A skin lesion imaged with a dermatoscope.
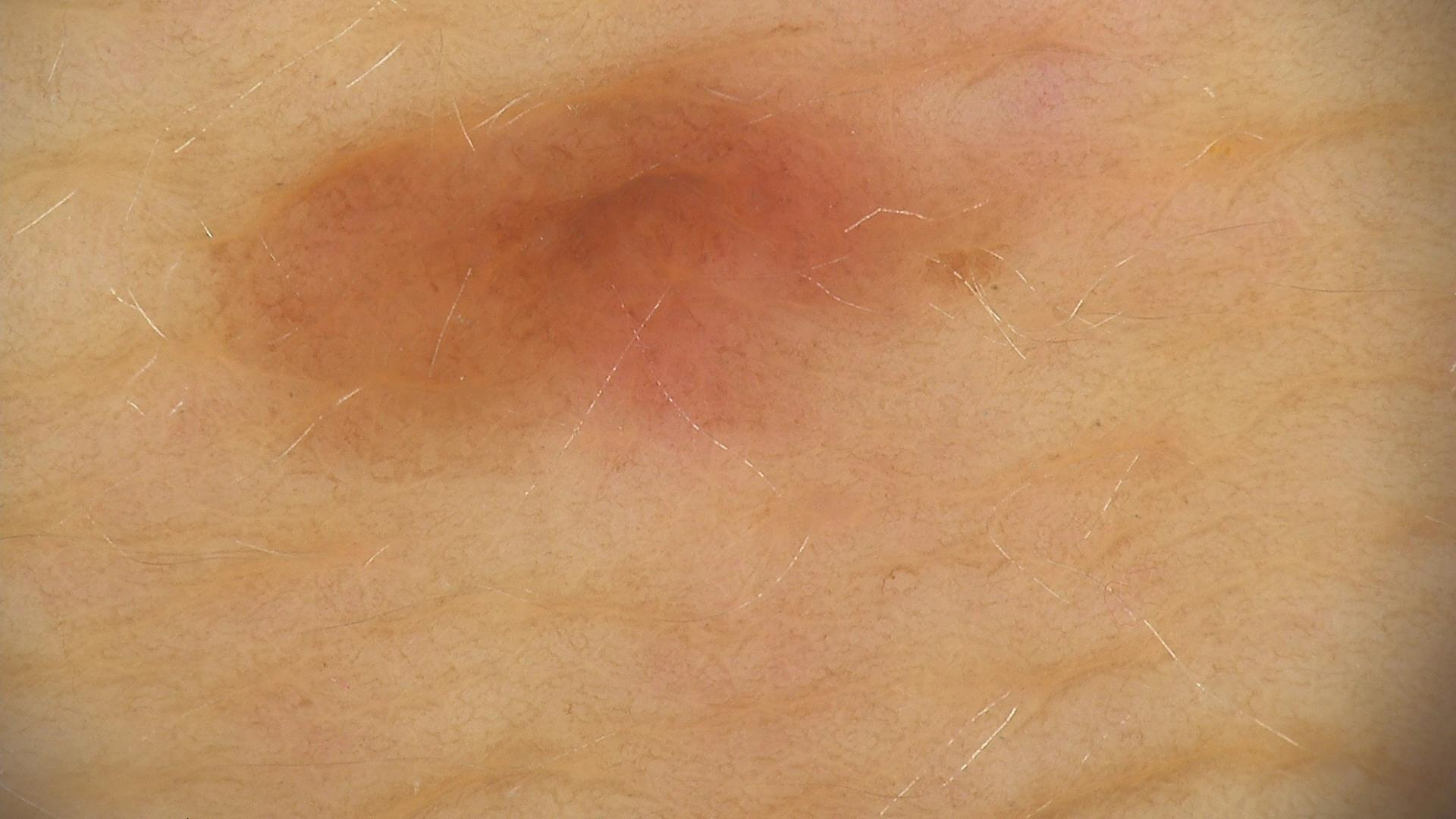Conclusion: The diagnosis was a compound nevus.